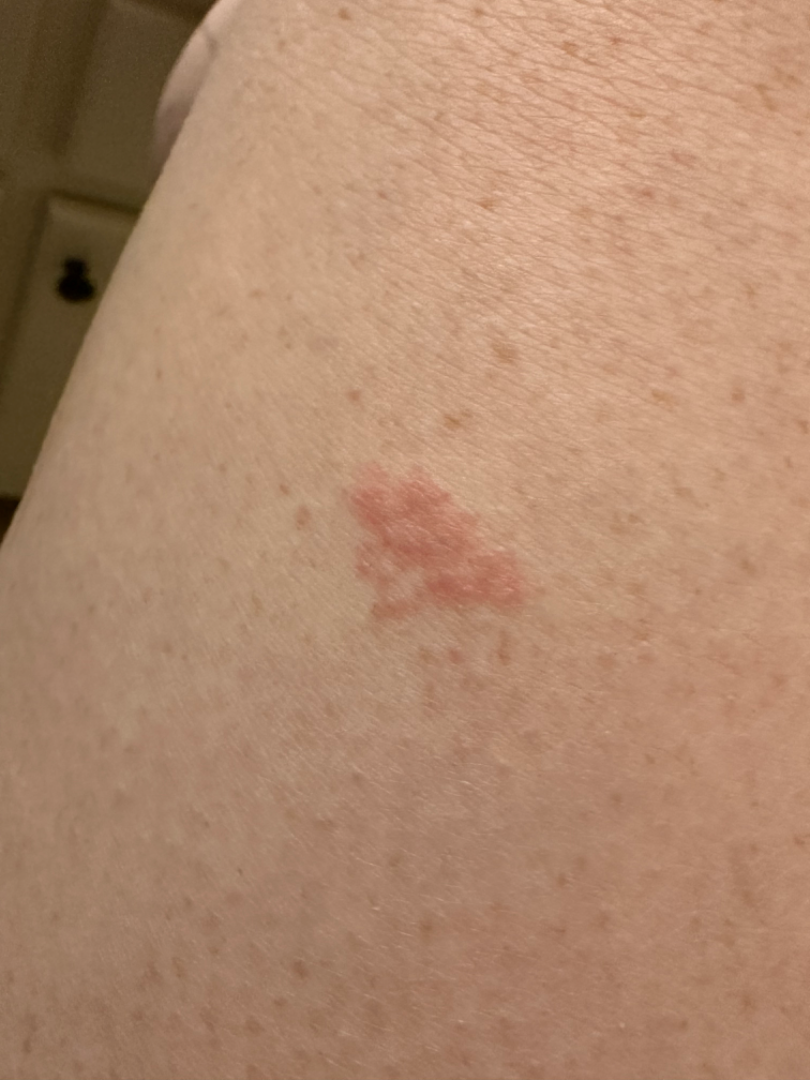  assessment: indeterminate from the photograph
  patient: female, age 18–29
  body_site: leg
  shot_type: at an angle